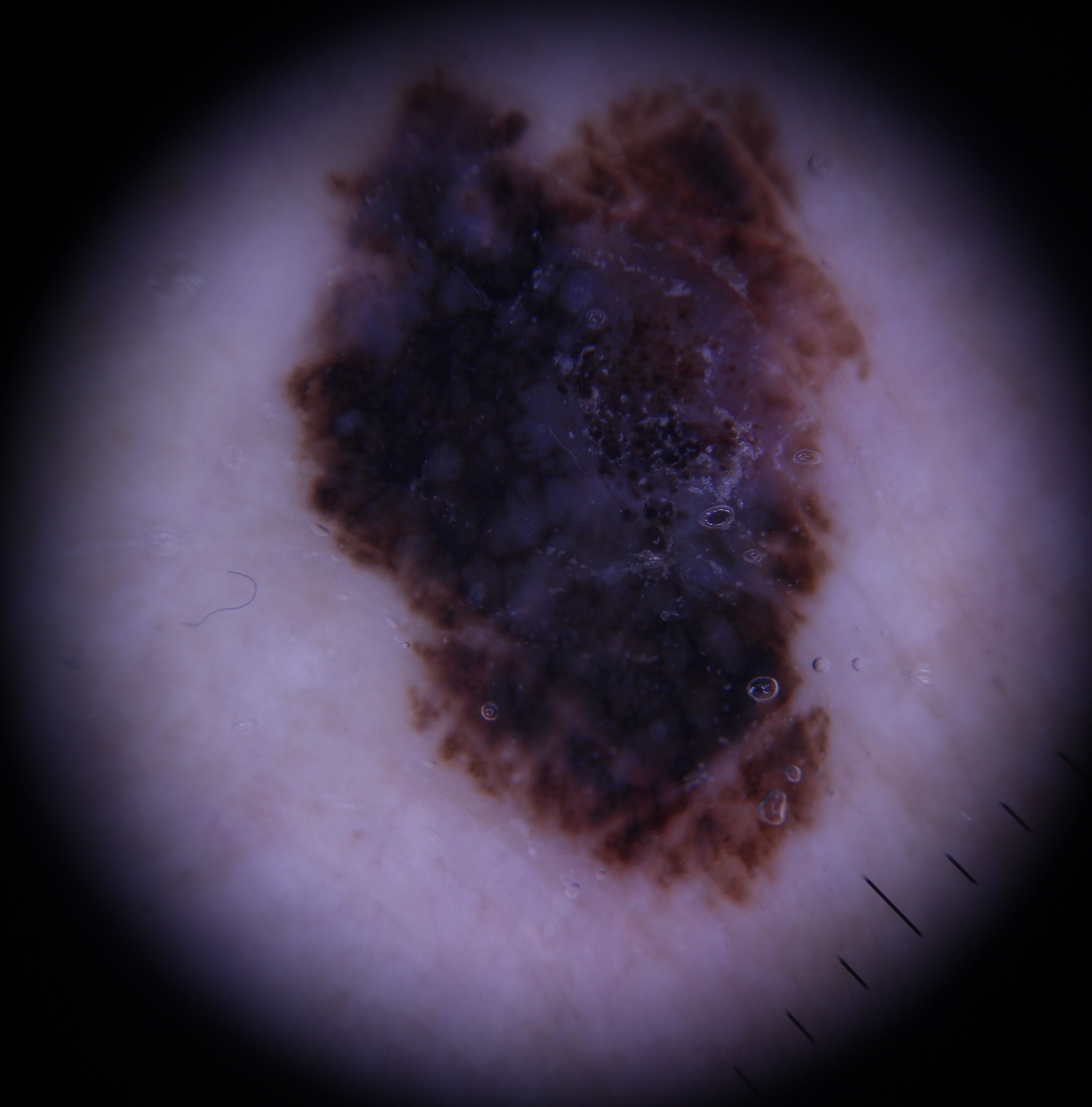A dermoscopic image of a skin lesion. The biopsy diagnosis was a melanoma.